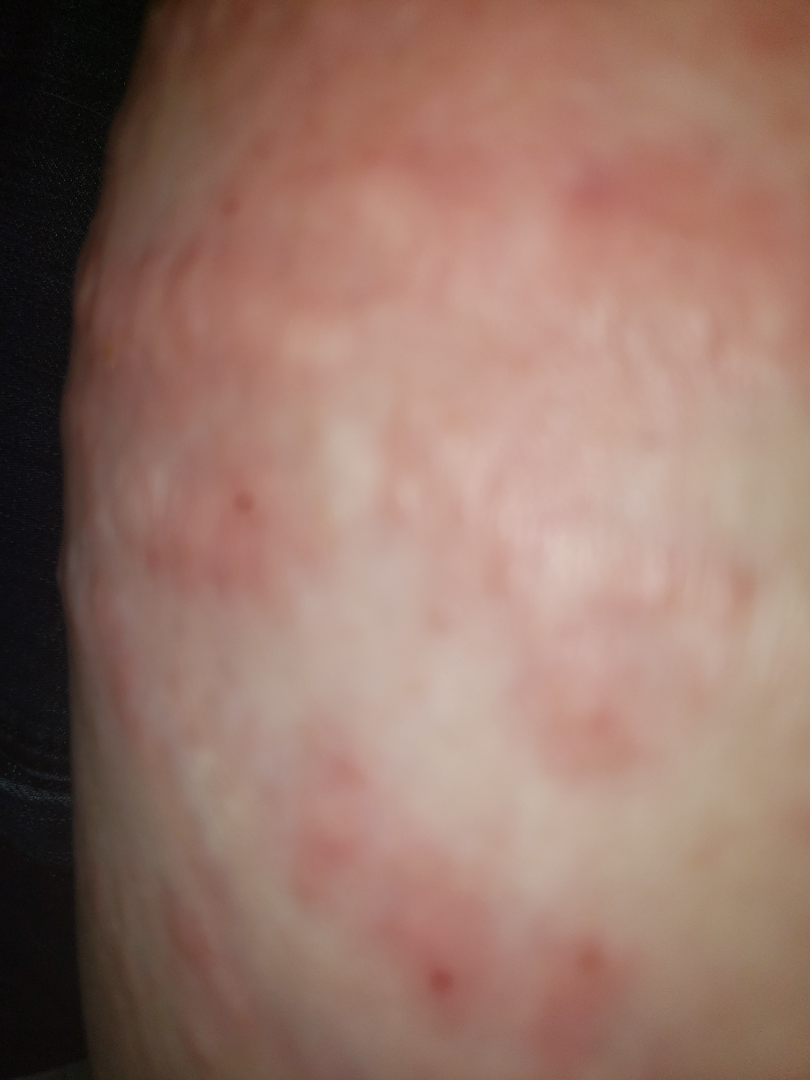assessment = unable to determine | image framing = at an angle | texture = raised or bumpy | subject = female, age 40–49 | constitutional symptoms = none reported | symptoms = itching and enlargement | present for = one to four weeks.